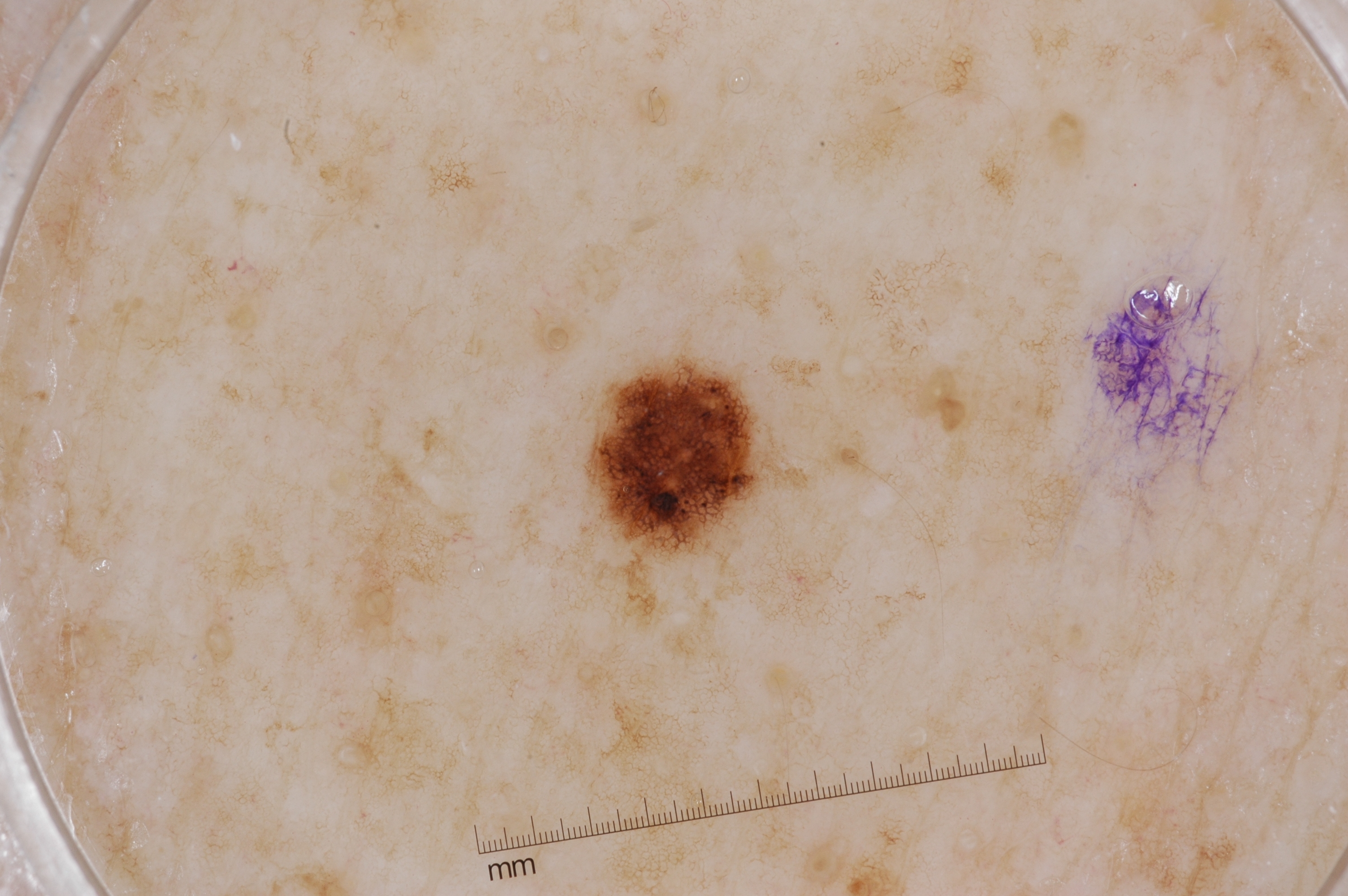Case summary: A dermoscopic view of a skin lesion. A female subject approximately 65 years of age. Dermoscopy demonstrates pigment network. The lesion takes up about 2% of the image. With coordinates (x1, y1, x2, y2), the lesion is bounded by <box>590, 364, 769, 546</box>. Assessment: Consistent with a melanocytic nevus, a benign skin lesion.